A female patient 67 years of age; acquired for a research image collection, with no referral diagnosis; the patient says their skin reddens with sun exposure; a clinical photograph of a skin lesion.
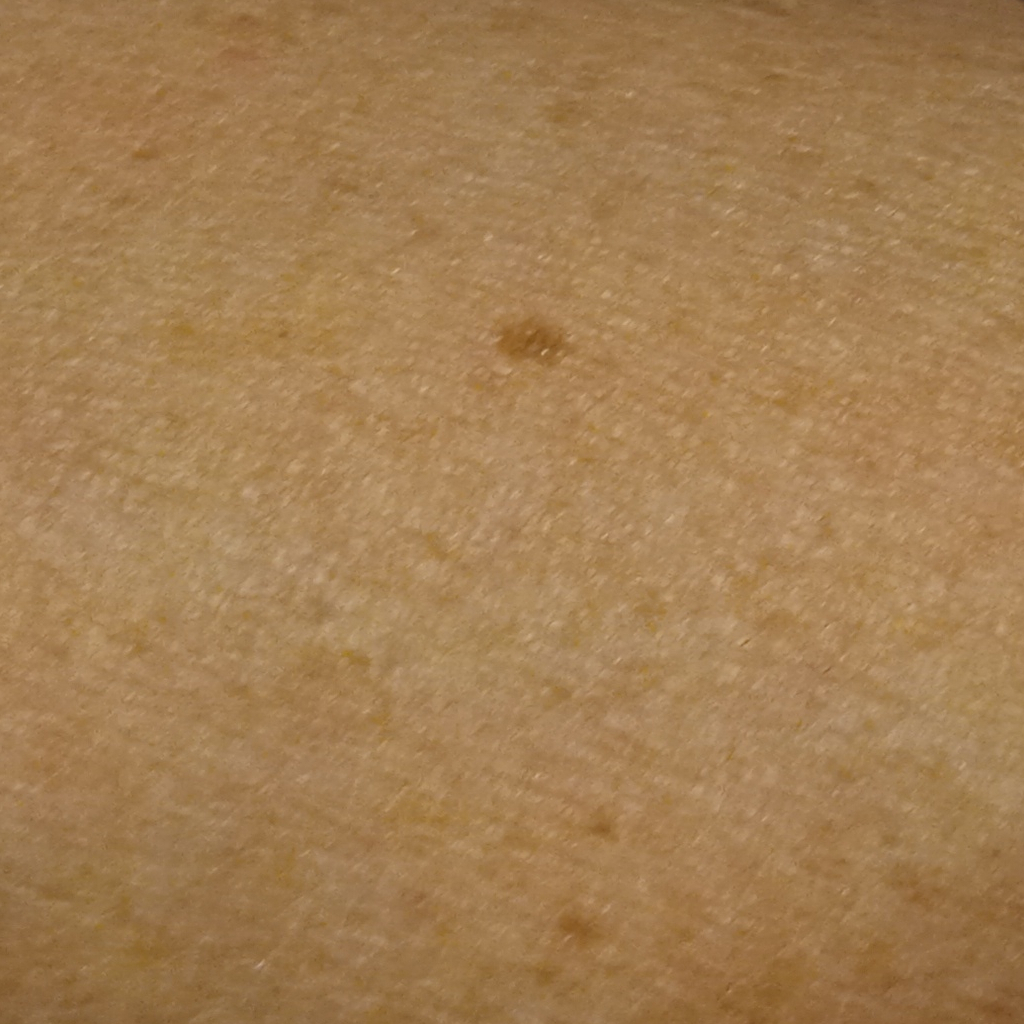Summary: The lesion is located on an arm. Impression: Dermatologist review favored a melanocytic nevus.